The affected area is the front of the torso, head or neck, palm, leg, arm and back of the torso · an image taken at a distance · the contributor is female.
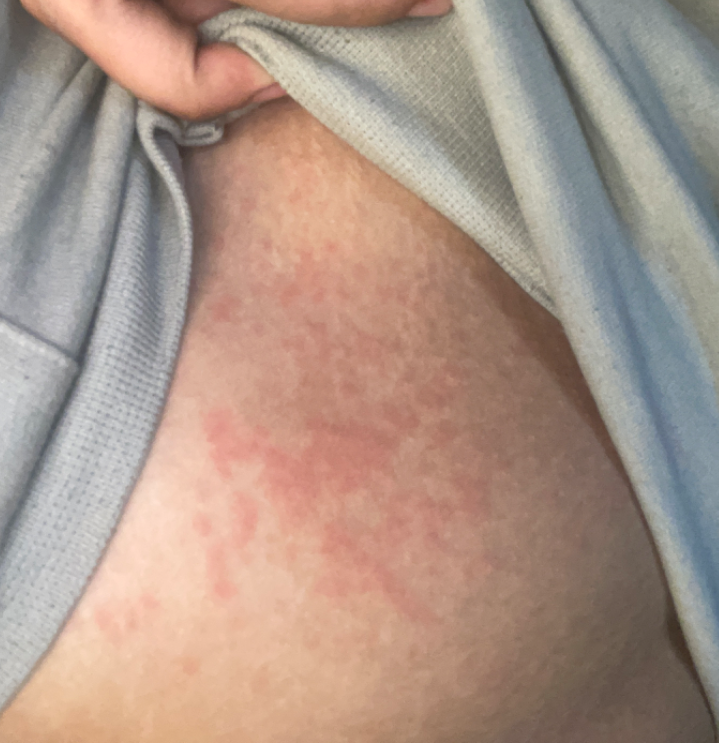On photographic review by a dermatologist: Urticaria (100%).